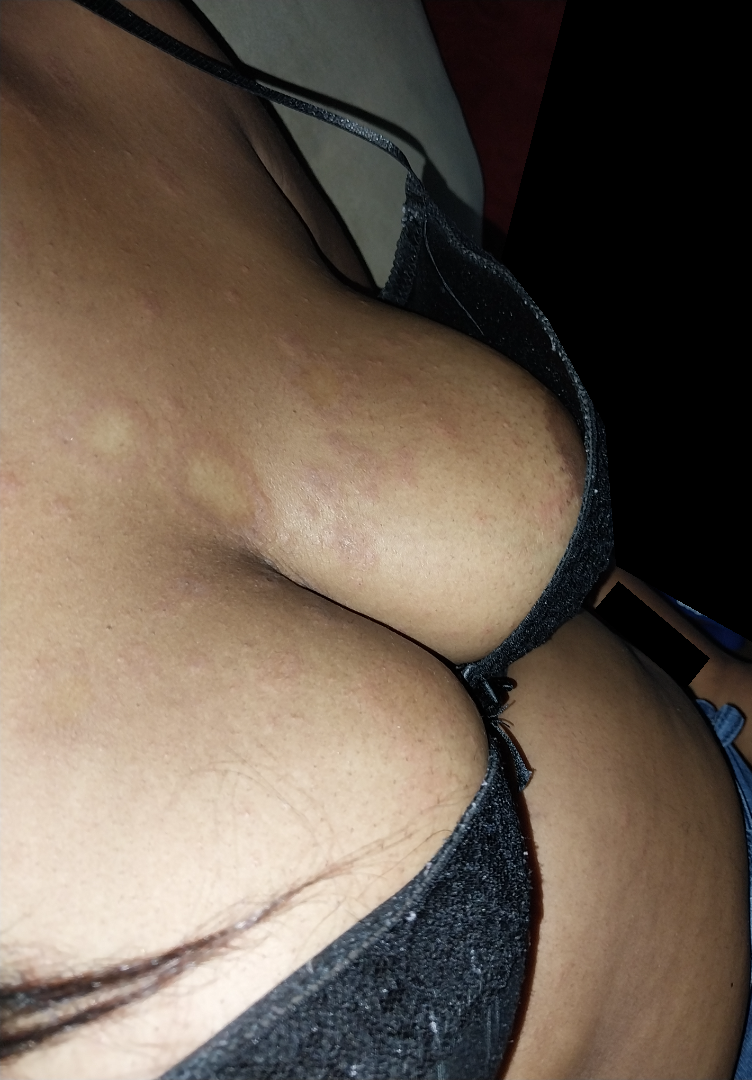Q: Constitutional symptoms?
A: fatigue
Q: Duration?
A: one to four weeks
Q: Texture?
A: raised or bumpy
Q: What symptoms does the patient report?
A: itching, darkening, enlargement and bothersome appearance
Q: Age and sex?
A: female, age 40–49
Q: What is the framing?
A: at an angle
Q: Patient's own categorization?
A: a rash
Q: What is the dermatologist's impression?
A: Scar Condition (considered); Pityriasis rosea (considered); Psoriasis (unlikely); Eczema (unlikely)